This image was taken at a distance; the lesion involves the arm.
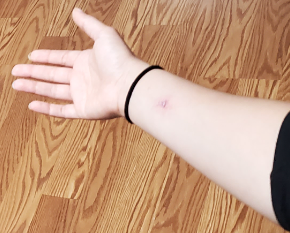On photographic review by a dermatologist, Impetigo and Allergic Contact Dermatitis were considered with similar weight.